A skin lesion imaged with a dermatoscope:
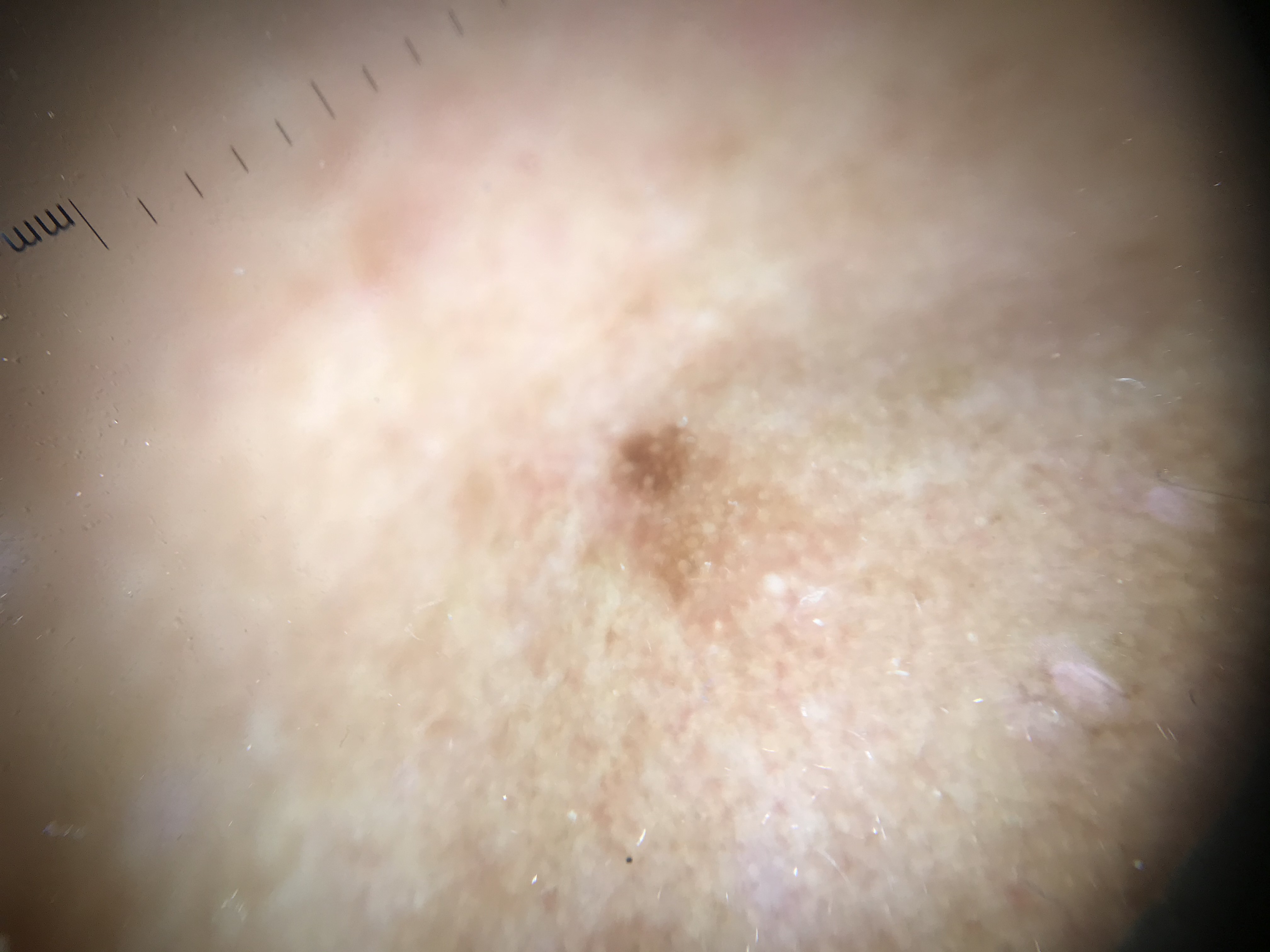assessment=seborrheic keratosis (expert consensus)